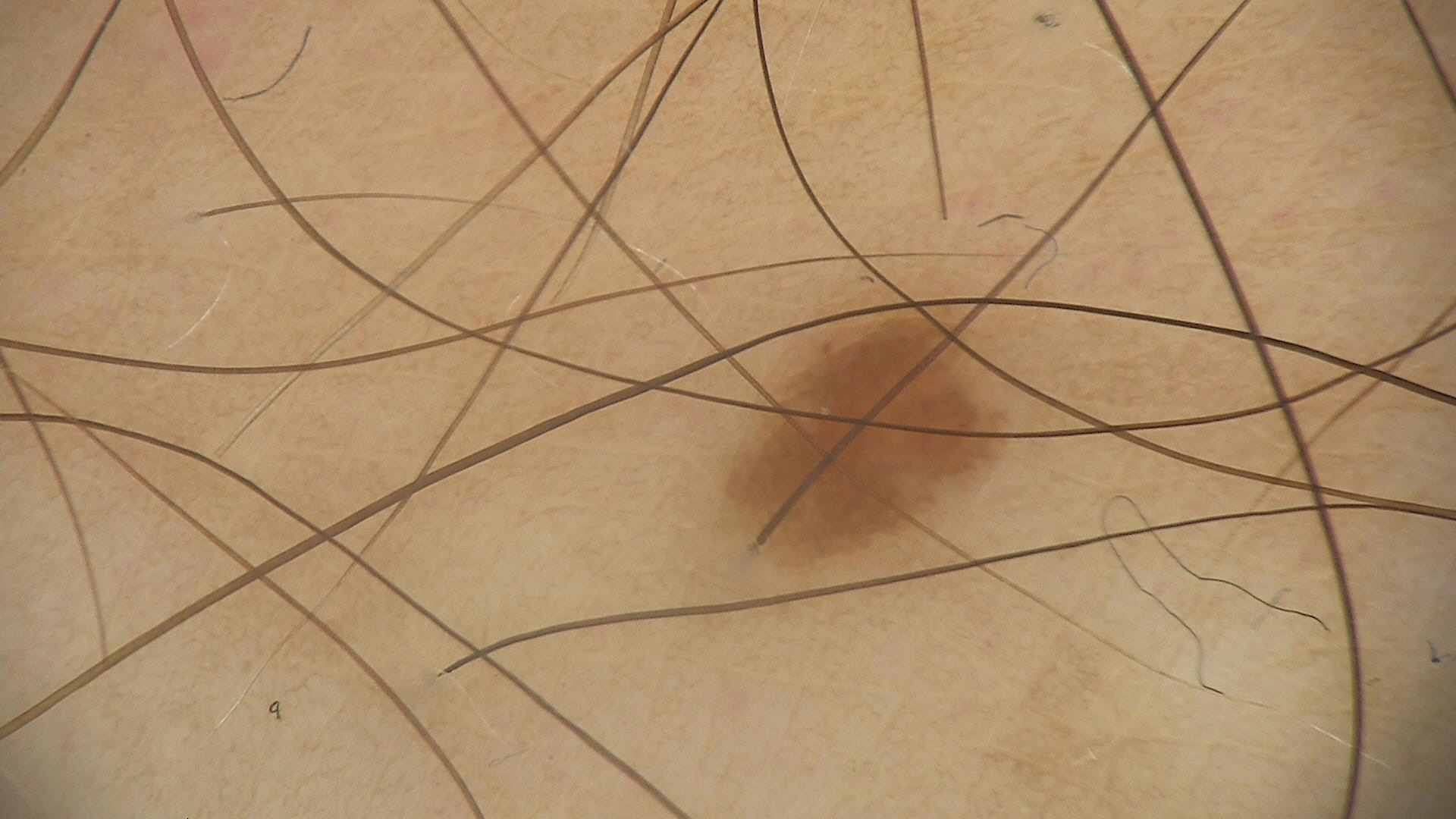{"image": "dermatoscopy", "lesion_type": {"main_class": "banal", "pattern": "junctional"}, "diagnosis": {"name": "junctional nevus", "code": "jb", "malignancy": "benign", "super_class": "melanocytic", "confirmation": "expert consensus"}}